The subject is 18–29, female; the back of the hand and arm are involved; this is a close-up image:
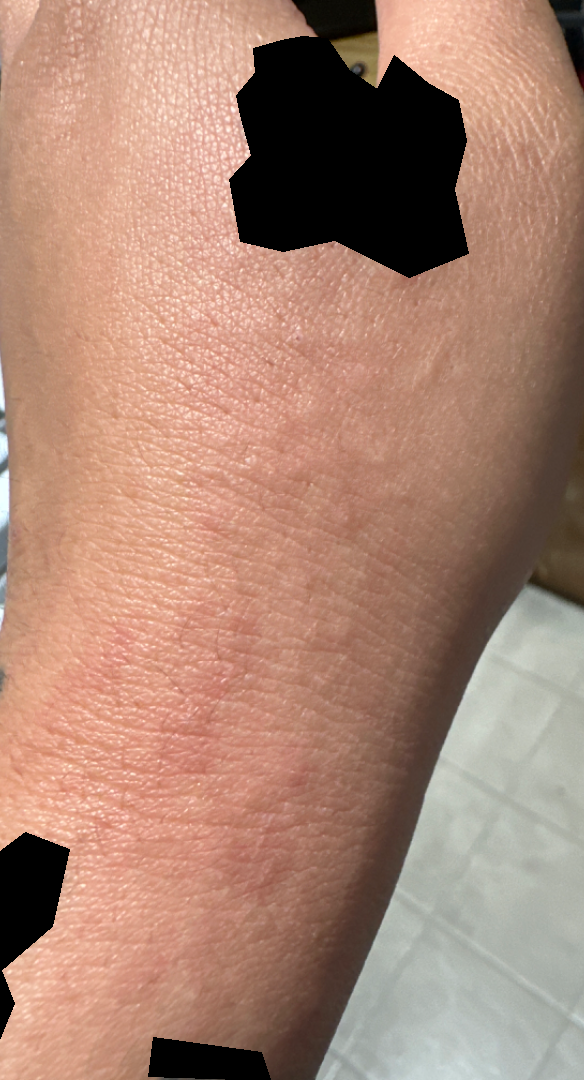Review:
On photographic review, Contact dermatitis and Allergic Contact Dermatitis were each considered, in no particular order.